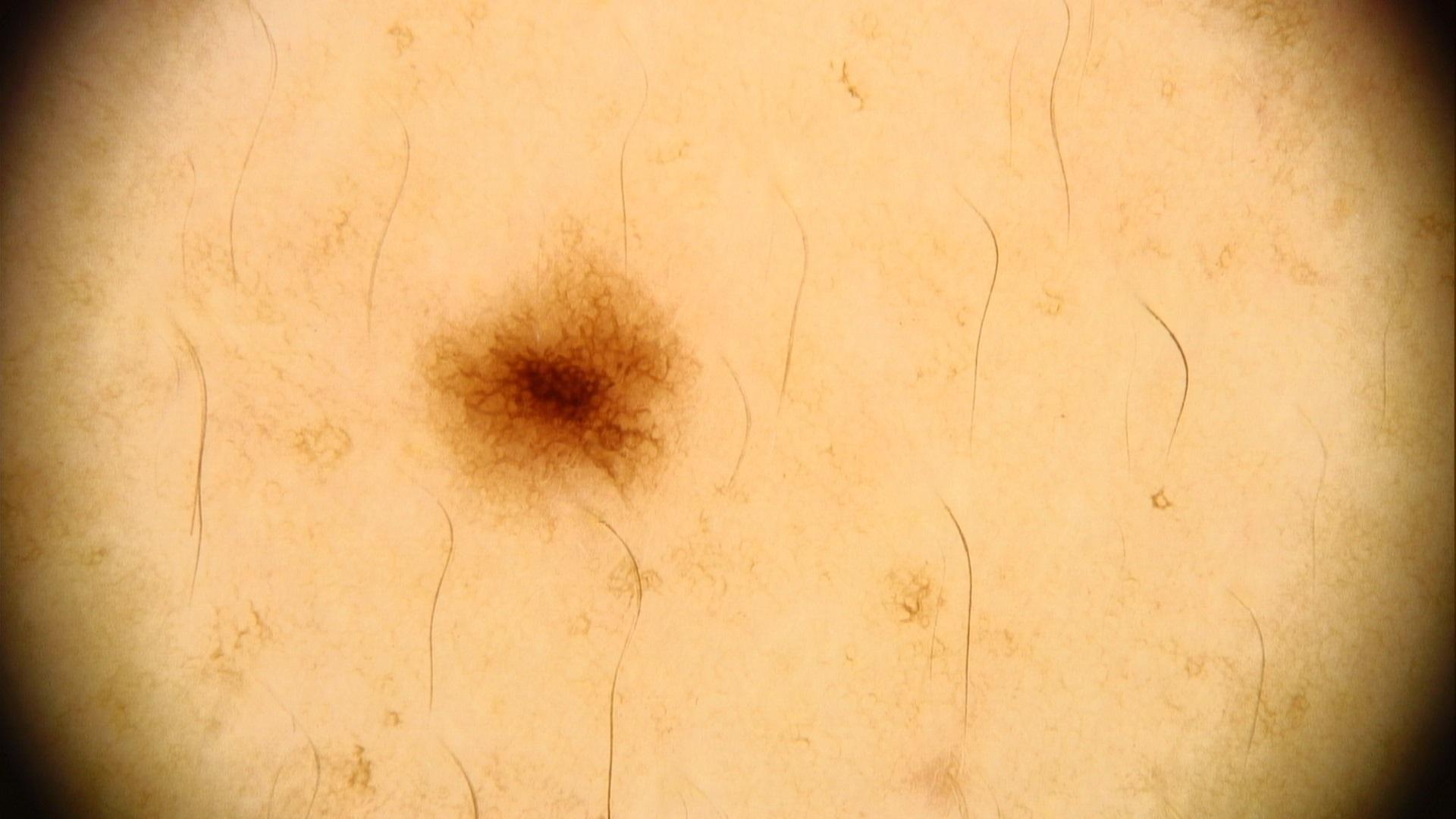imaging: contact-polarized dermoscopy; FST: III; patient: male, aged 38-42; site: the trunk, specifically the posterior trunk; diagnosis: Nevus (clinical impression).